A clinical close-up photograph of a skin lesion · a patient 64 years old: 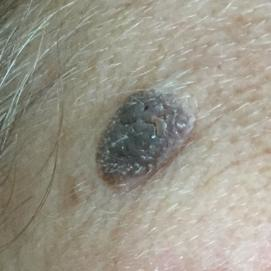Summary:
The lesion was found on the face. Per patient report, the lesion is elevated and has grown.
Conclusion:
The consensus clinical diagnosis was a seborrheic keratosis.